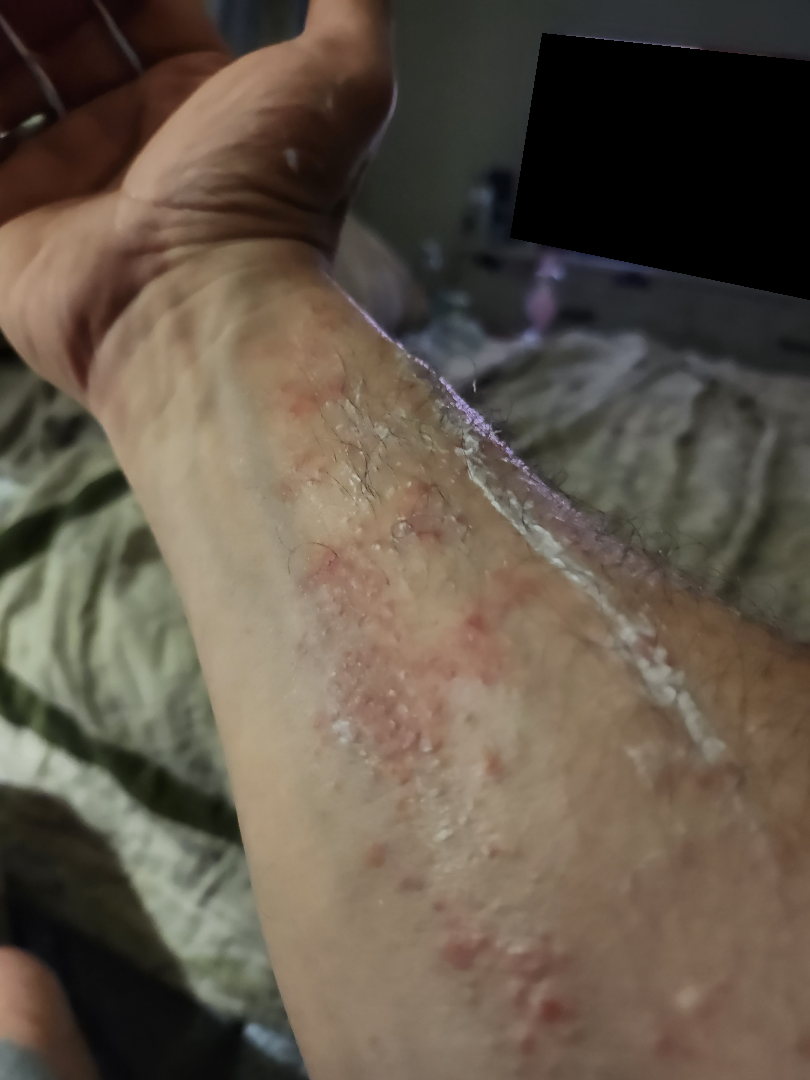Clinical context:
This image was taken at an angle. Located on the arm. The subject is a male aged 50–59.
Assessment:
The reviewing dermatologists' impression was: most likely Allergic Contact Dermatitis; also consider Scabies; also on the differential is Insect Bite.